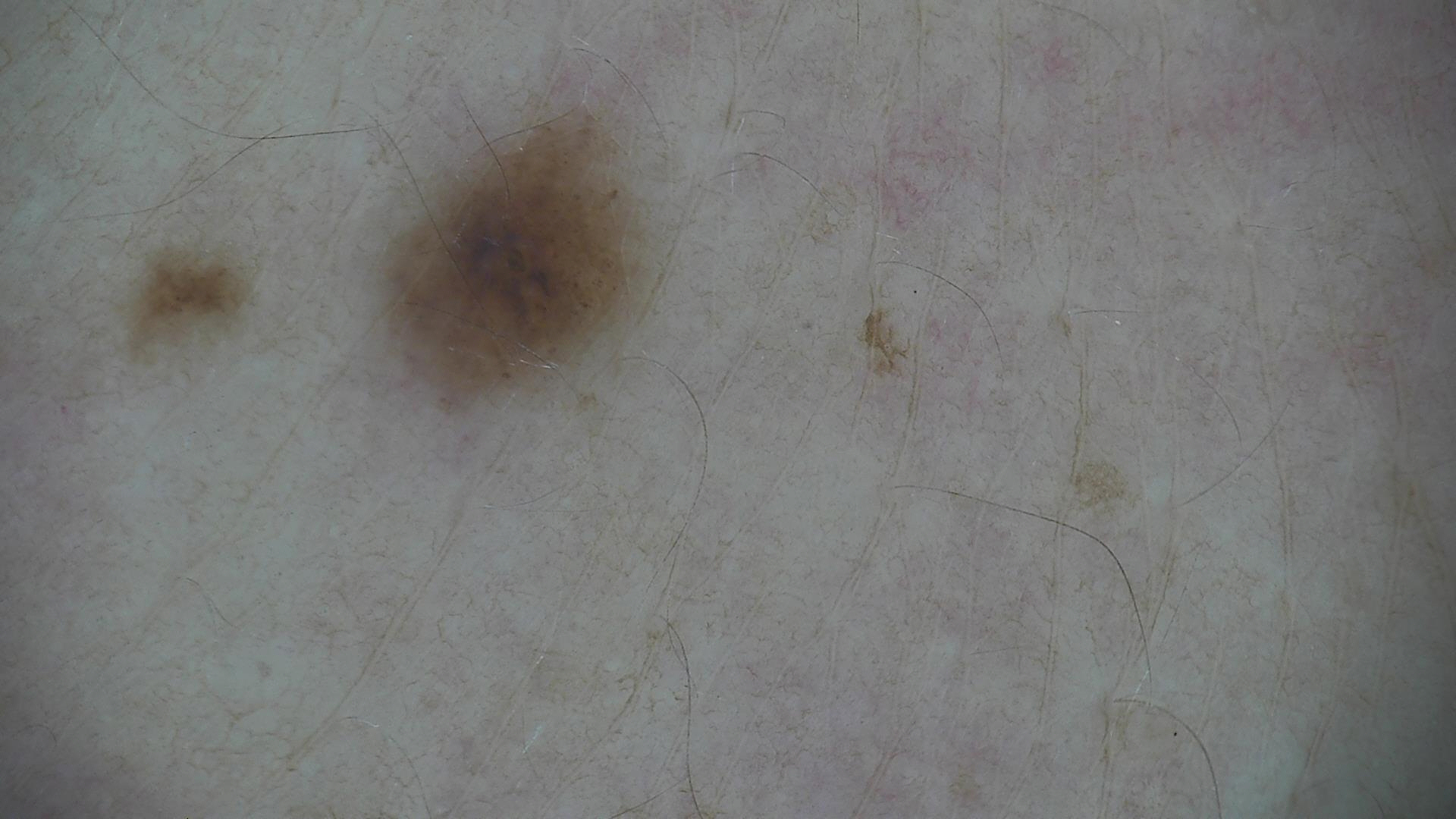• image — dermoscopy
• diagnostic label — dysplastic junctional nevus (expert consensus)